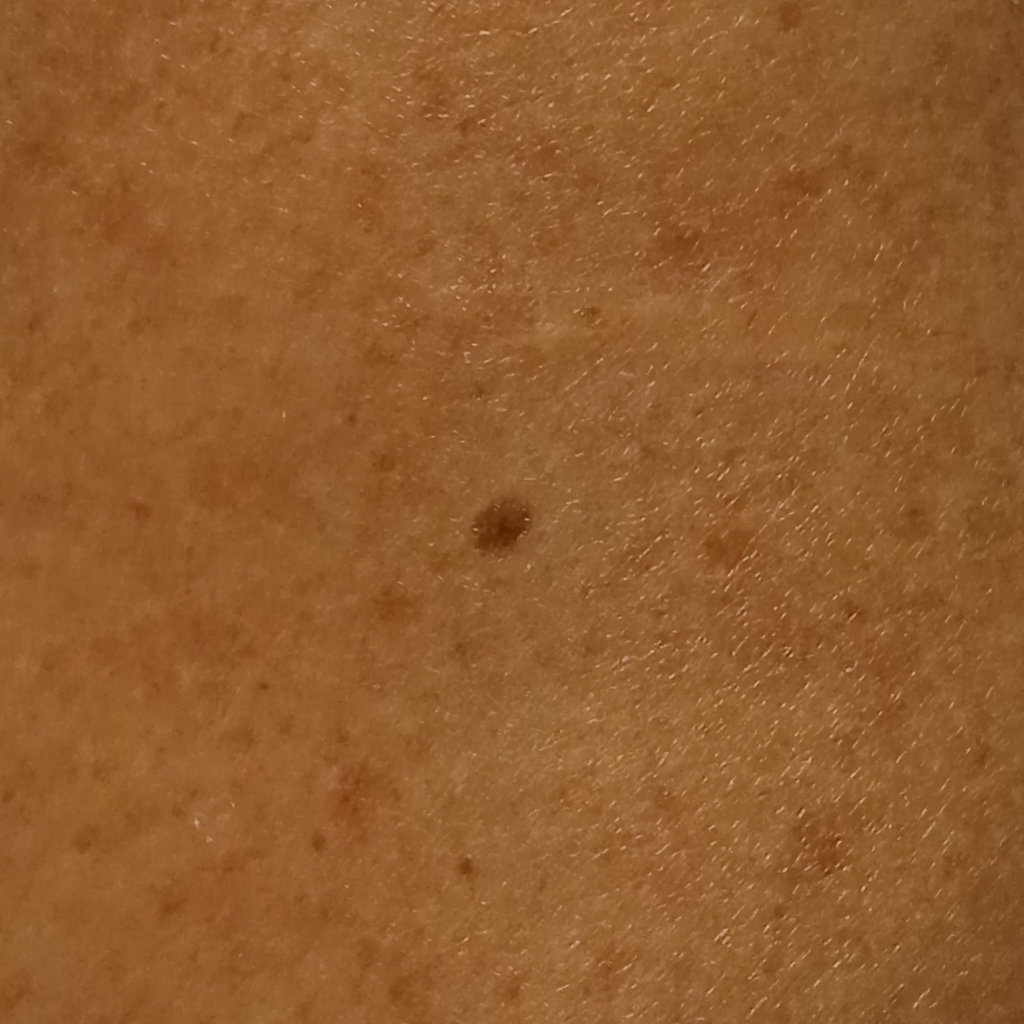Acquired for a research image collection, with no referral diagnosis. A male subject 72 years of age. A moderate number of moles by the patient's own estimate. A clinical photograph of a skin lesion. The lesion involves the back. Measuring roughly 3.7 mm. The consensus diagnosis for this lesion was a melanocytic nevus.